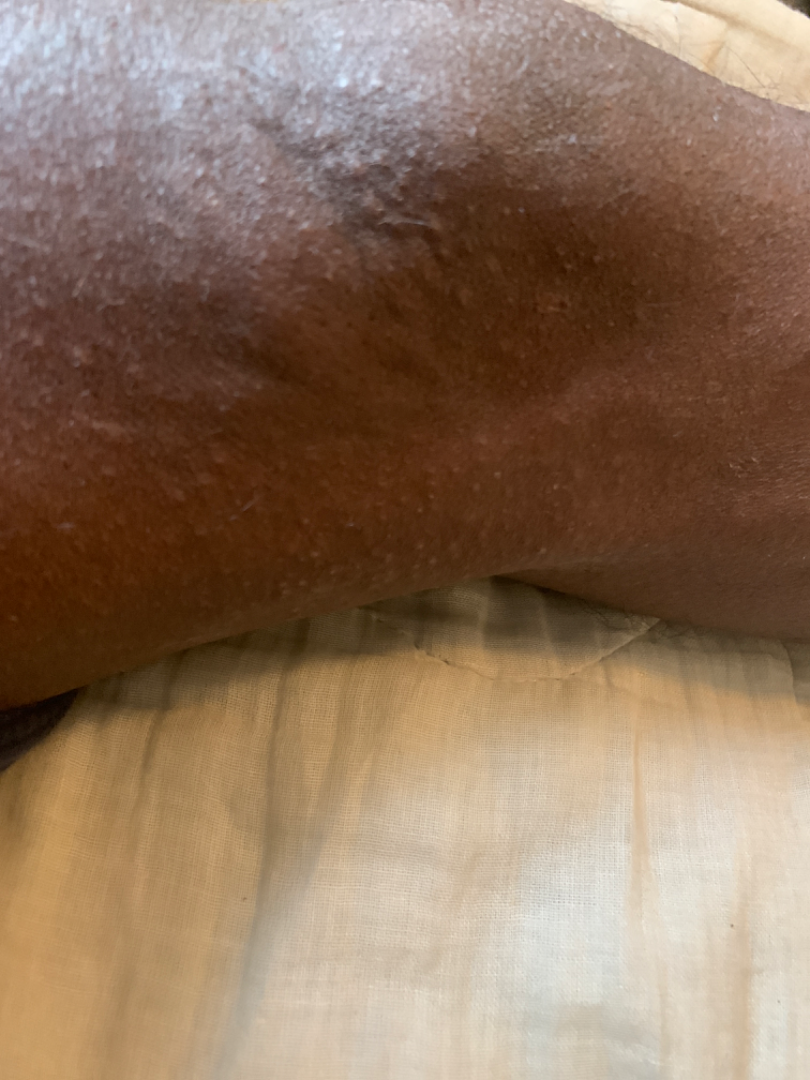view — at an angle | patient — male, age 18–29 | present for — less than one week | lesion texture — raised or bumpy and fluid-filled | patient's own categorization — a rash | location — arm, leg and back of the hand | symptoms — bothersome appearance, itching and burning | differential — three dermatologists independently reviewed the case: consistent with Eczema.